A close-up photograph: 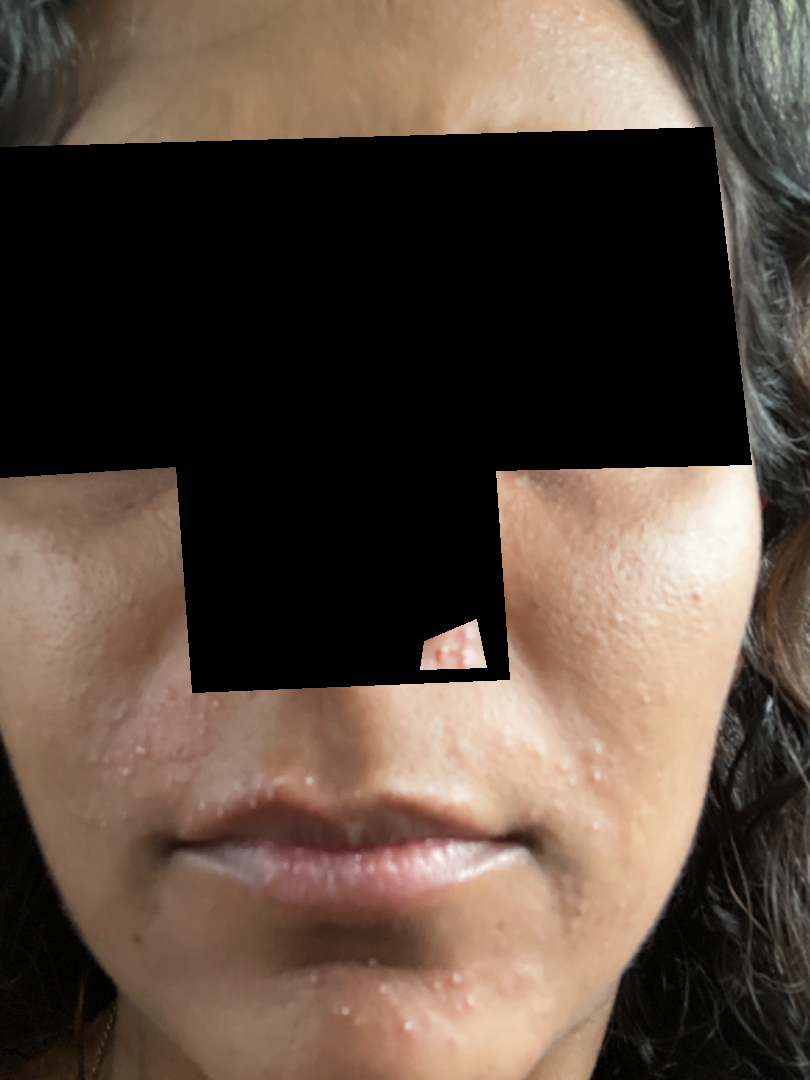History:
Skin tone: Fitzpatrick skin type IV; non-clinician graders estimated MST 4 (US pool) or 2 (India pool).
Impression:
On remote review of the image, Acne (considered); Milia (considered); Perioral Dermatitis (considered).